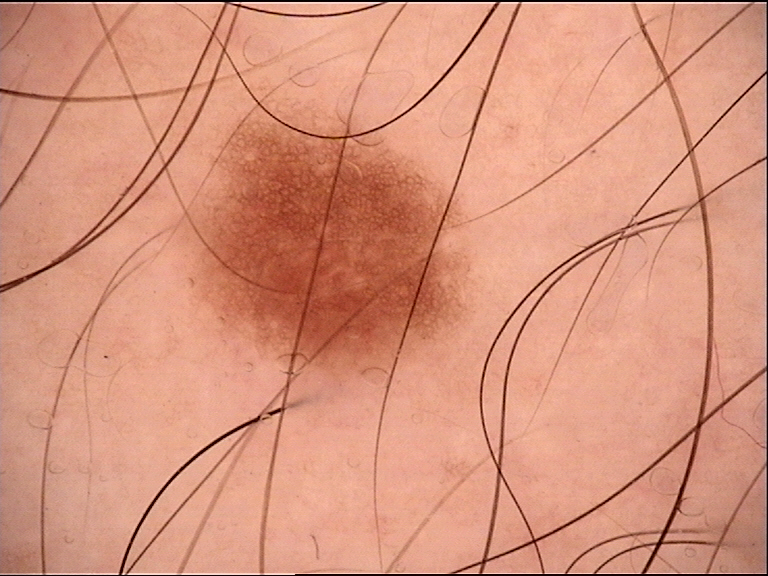A dermatoscopic image of a skin lesion.
Labeled as a dysplastic junctional nevus.